The affected area is the leg. A close-up photograph:
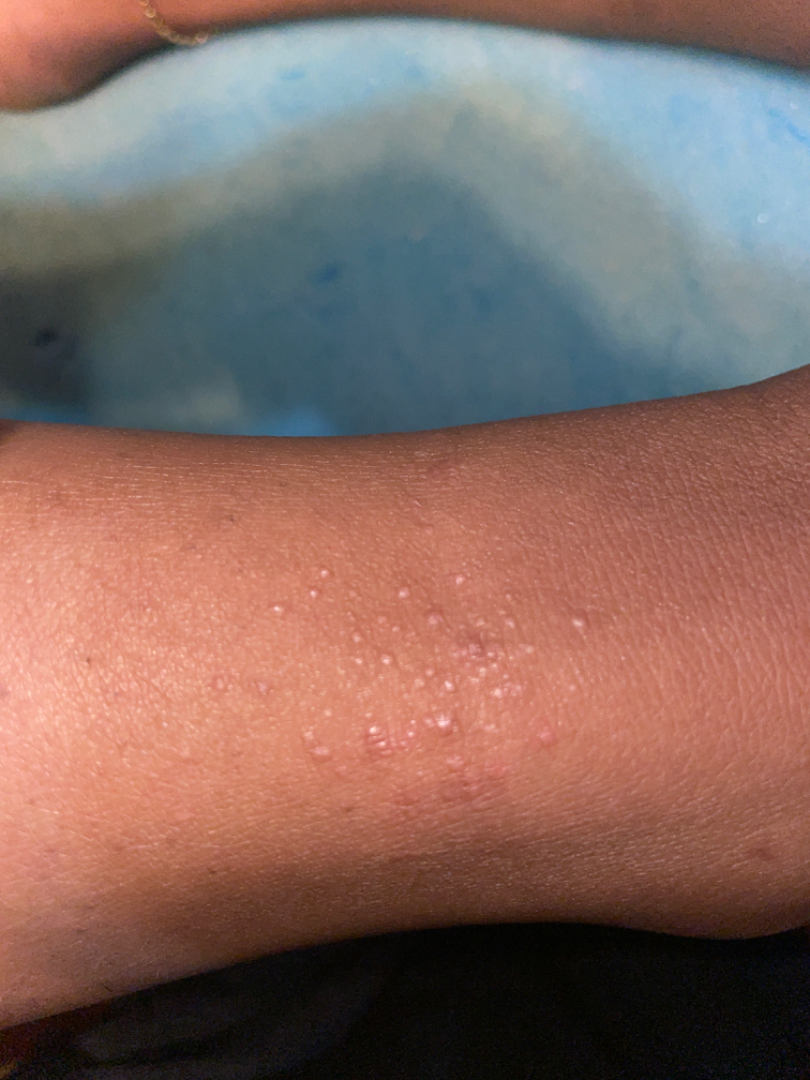<case>
<duration>one to three months</duration>
<differential>
  <leading>Eczema</leading>
  <considered>Lichen planus/lichenoid eruption</considered>
  <unlikely>Lichen nitidus, Allergic Contact Dermatitis, Lichen spinulosus</unlikely>
</differential>
</case>